Close-up view:
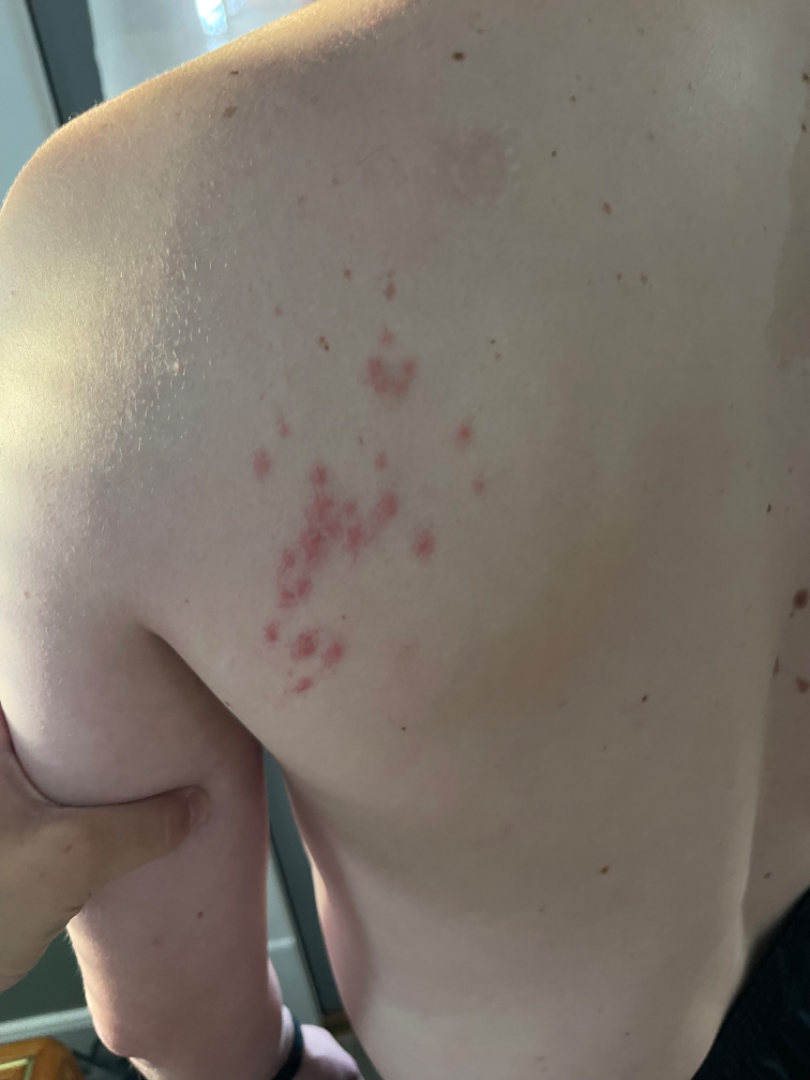The lesion is associated with itching. The patient considered this a rash. The patient reported no systemic symptoms. The patient notes the lesion is raised or bumpy. Fitzpatrick skin type III; non-clinician graders estimated Monk skin tone scale 1–2. The condition has been present for about one day. Most likely Herpes Zoster; also on the differential is Folliculitis.